A dermoscopic view of a skin lesion.
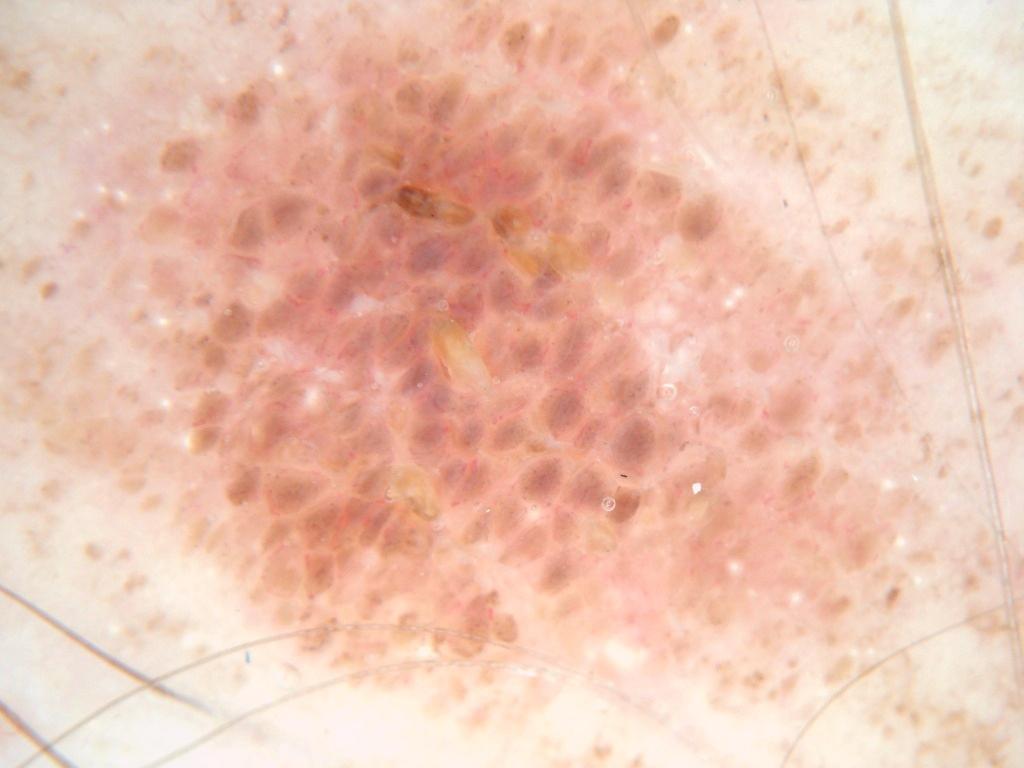Findings:
The lesion extends across almost the whole field of view.
Impression:
The lesion was assessed as a benign lesion.